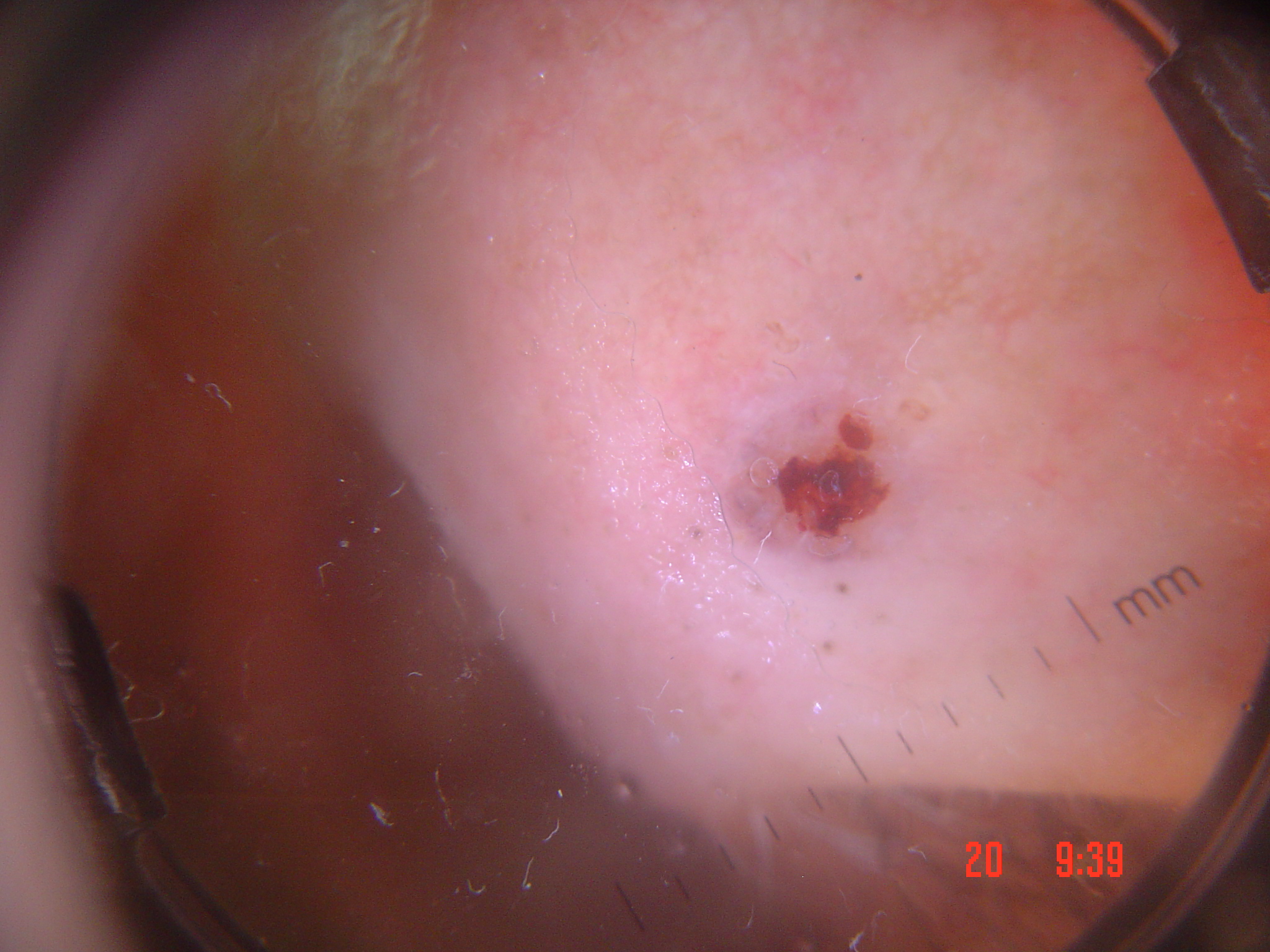Summary: A dermatoscopic image of a skin lesion. The architecture is that of a keratinocytic lesion. Conclusion: Histopathology confirmed a squamous cell carcinoma.